A dermoscopic photograph of a skin lesion.
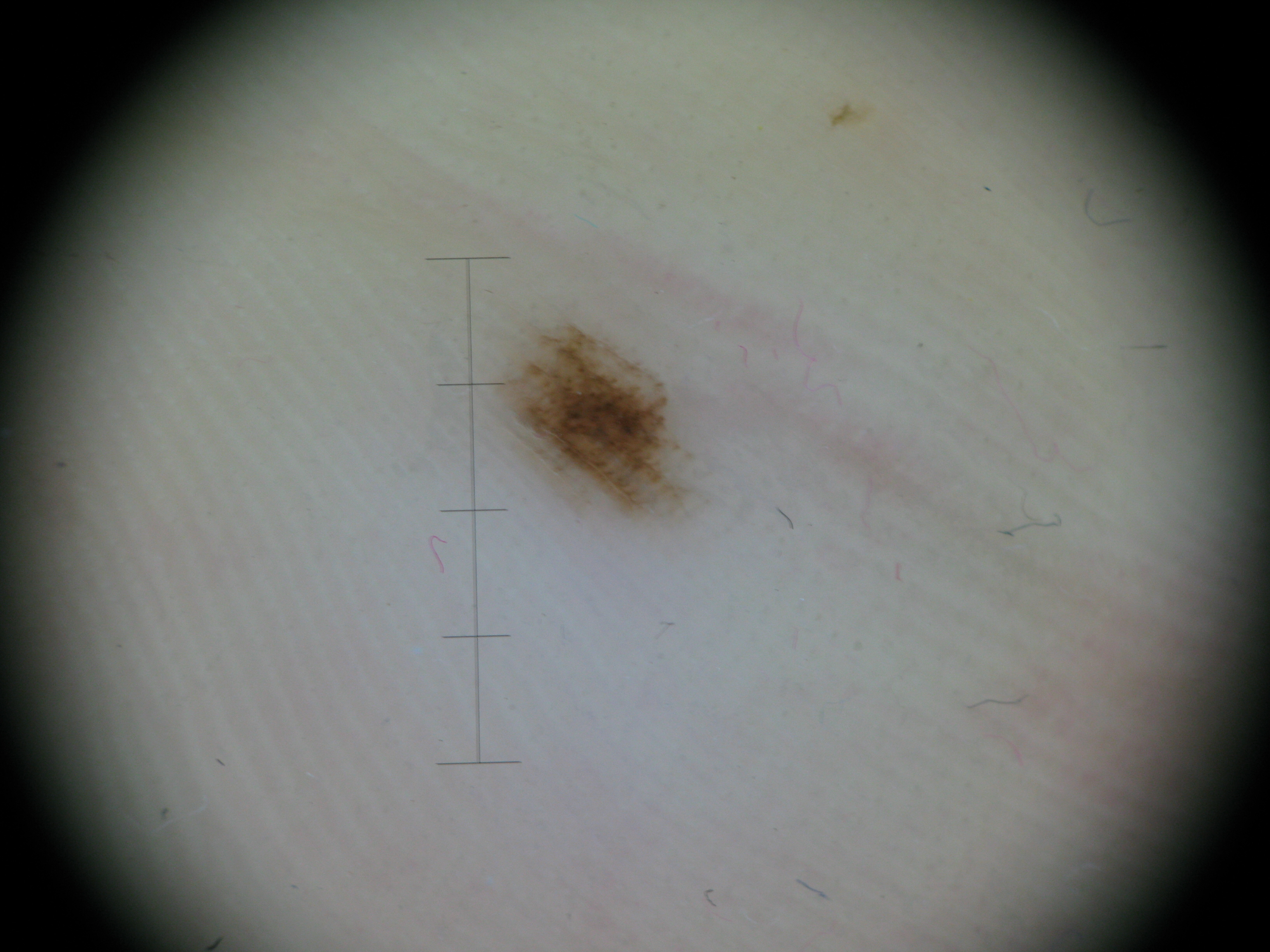| field | value |
|---|---|
| classification | banal |
| label | acral junctional nevus (expert consensus) |